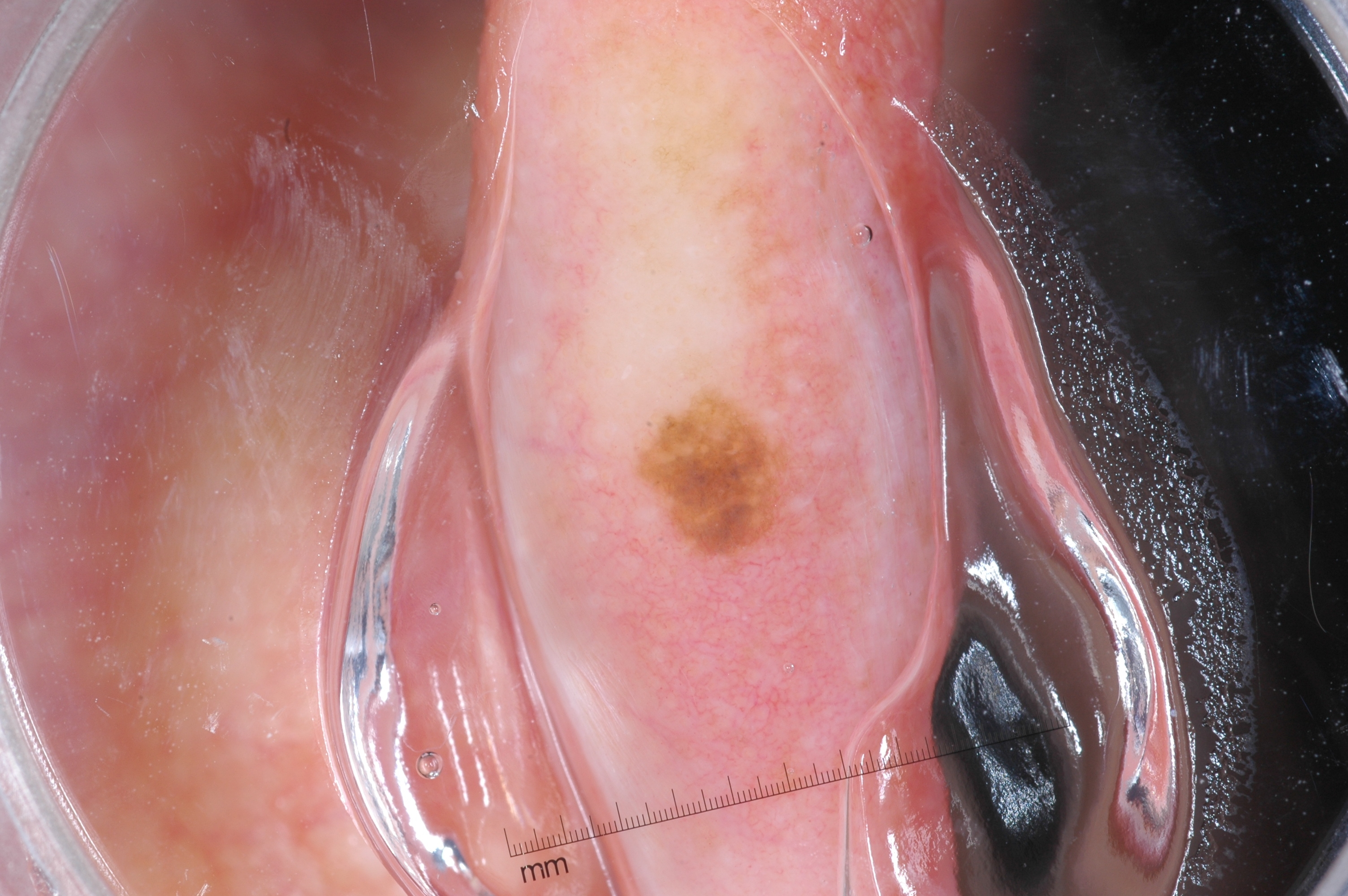A female patient roughly 45 years of age. A dermoscopic image of a skin lesion. Dermoscopy demonstrates no streaks, pigment network, negative network, or milia-like cysts. The lesion is small relative to the field of view. The lesion occupies the region box(635, 397, 805, 573). Clinically diagnosed as a melanocytic nevus.